The contributor is a female aged 30–39. The front of the torso, leg and arm are involved. This image was taken at an angle — 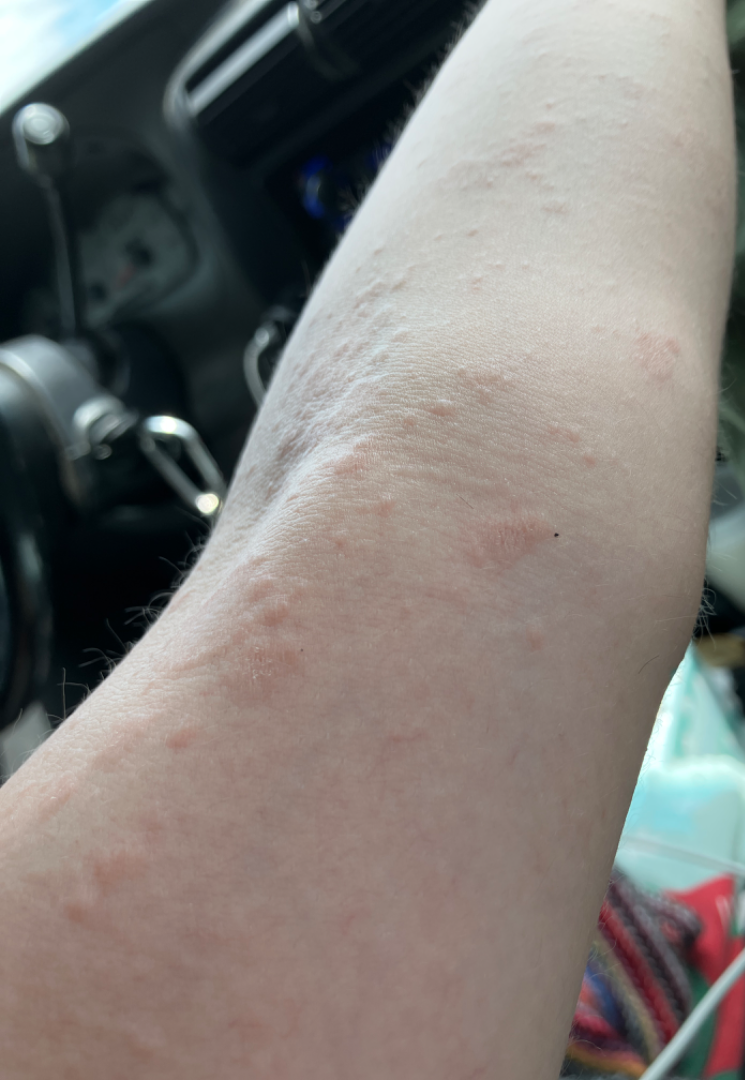dermatologist impression=the favored diagnosis is Urticaria; less likely is Tinea Versicolor; less probable is Allergic Contact Dermatitis; lower on the differential is Eczema